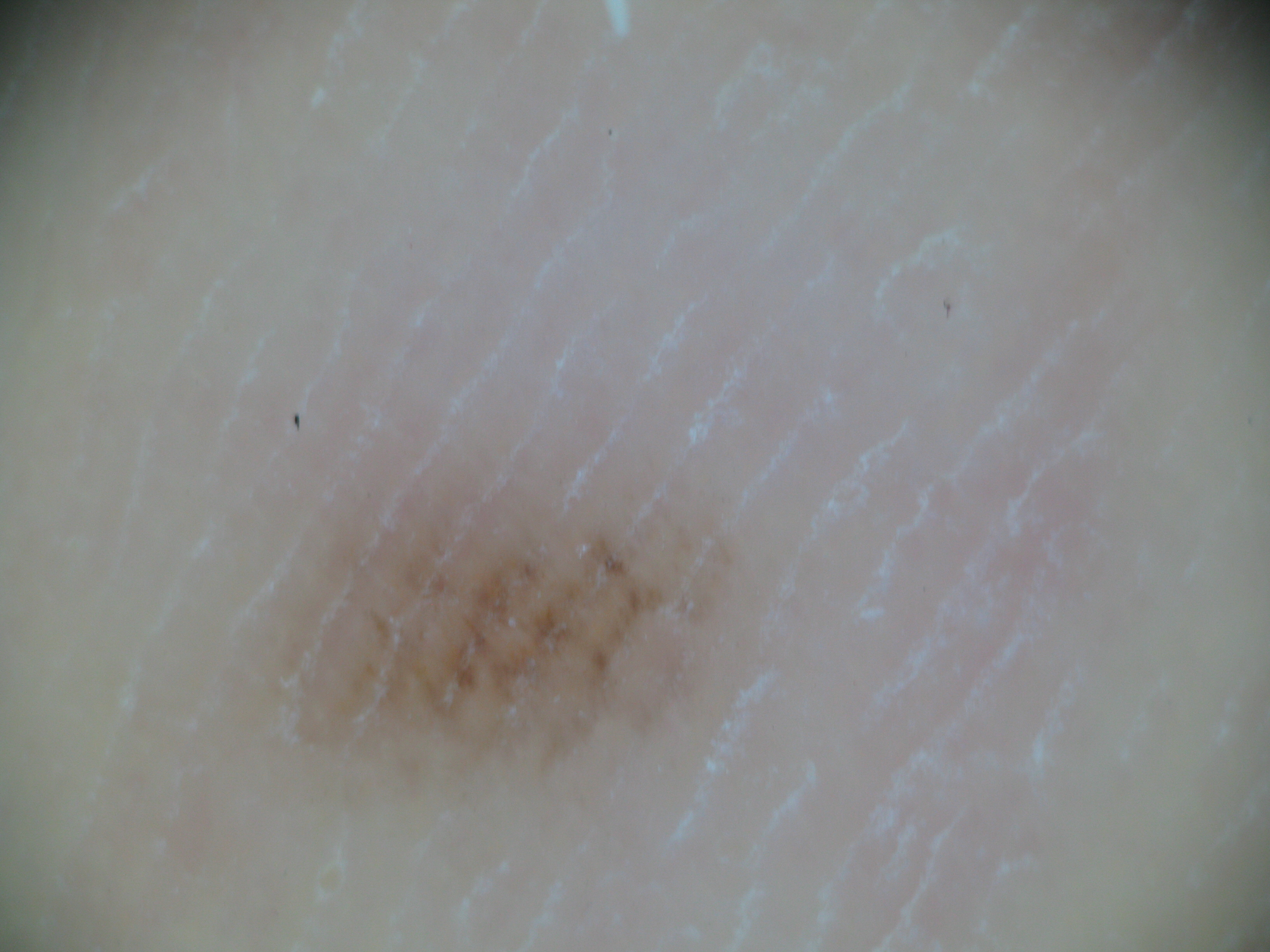Q: What is the diagnosis?
A: acral junctional nevus (expert consensus)